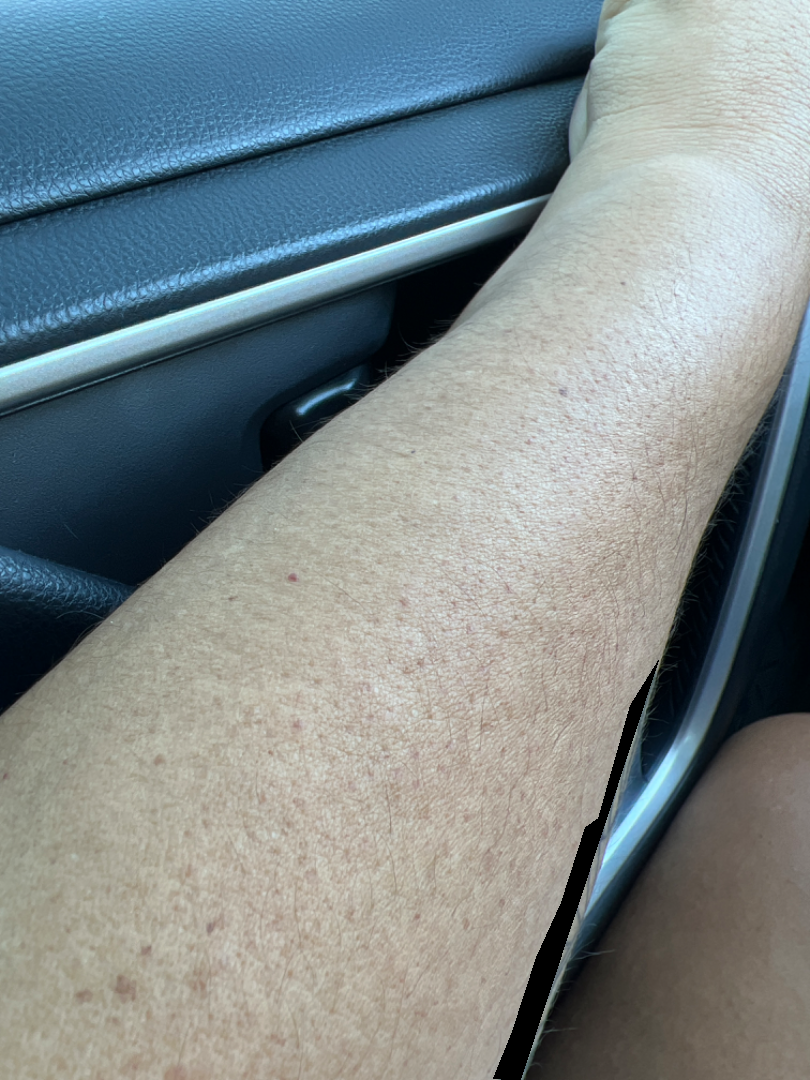The condition could not be reliably identified from the image.
The condition has been present for about one day.
A close-up photograph.
The lesion involves the arm and leg.
The patient reported no relevant symptoms from the lesion.
The patient considered this a rash.